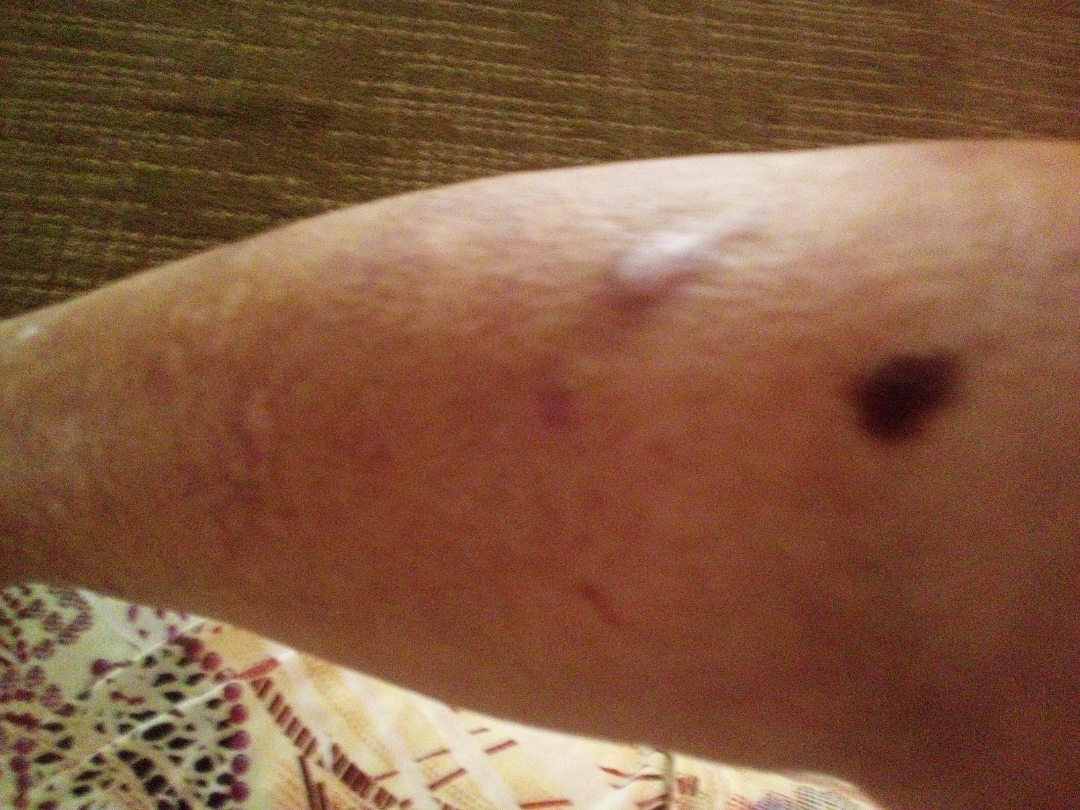Diagnostic features were not clearly distinguishable in this photograph. The arm is involved. The contributor is a female aged 50–59. The patient notes the lesion is raised or bumpy. The photograph is a close-up of the affected area. The patient notes darkening, pain, itching and bothersome appearance. Skin tone: self-reported Fitzpatrick III; human graders estimated Monk Skin Tone 4 (US pool) or 3 (India pool). Present for more than one year. The patient considered this a rash.